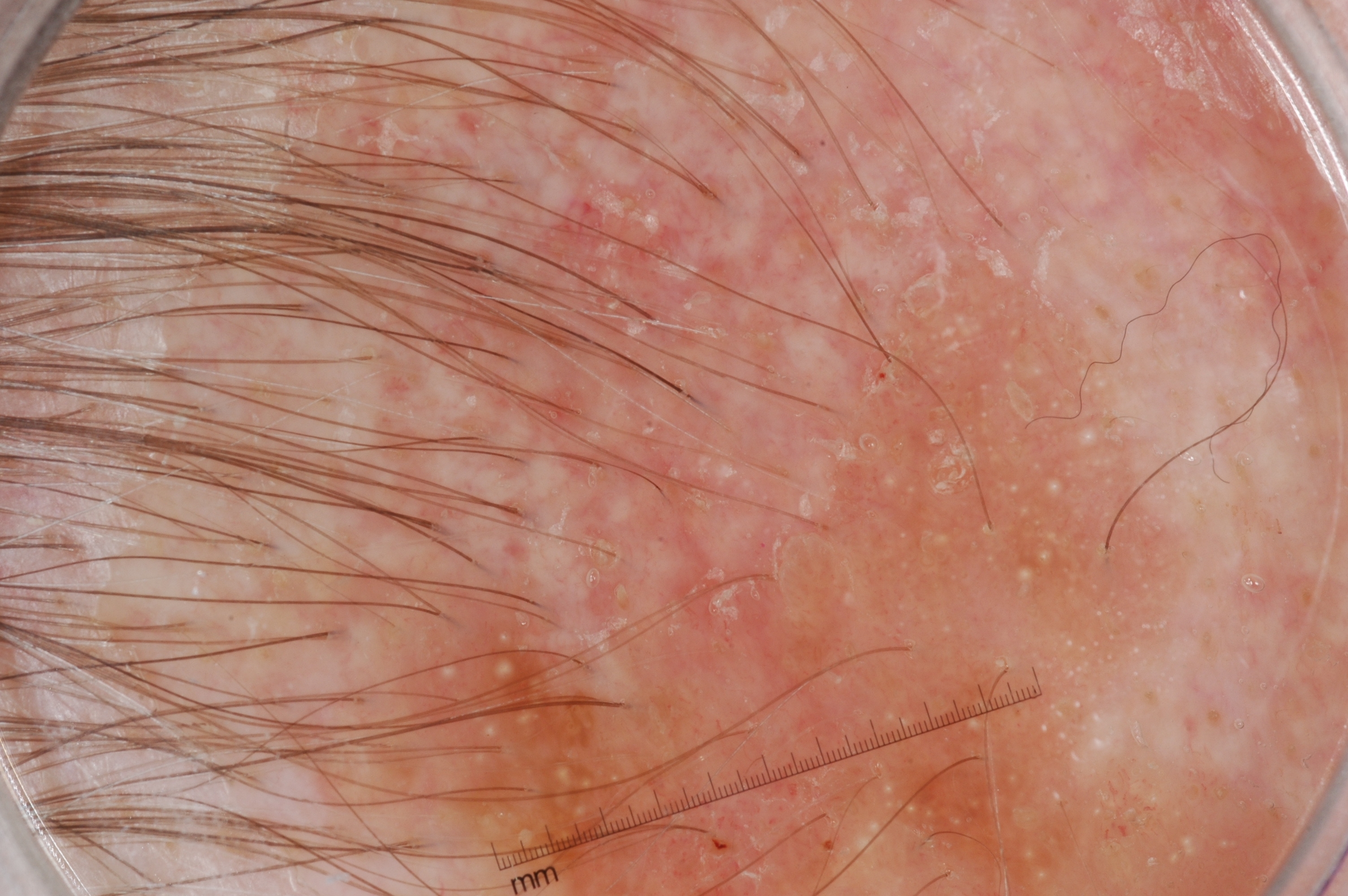A dermoscopic view of a skin lesion. Dermoscopic review identifies milia-like cysts. In (x1, y1, x2, y2) order, the visible lesion spans bbox(403, 129, 1303, 892). The lesion was assessed as a seborrheic keratosis.